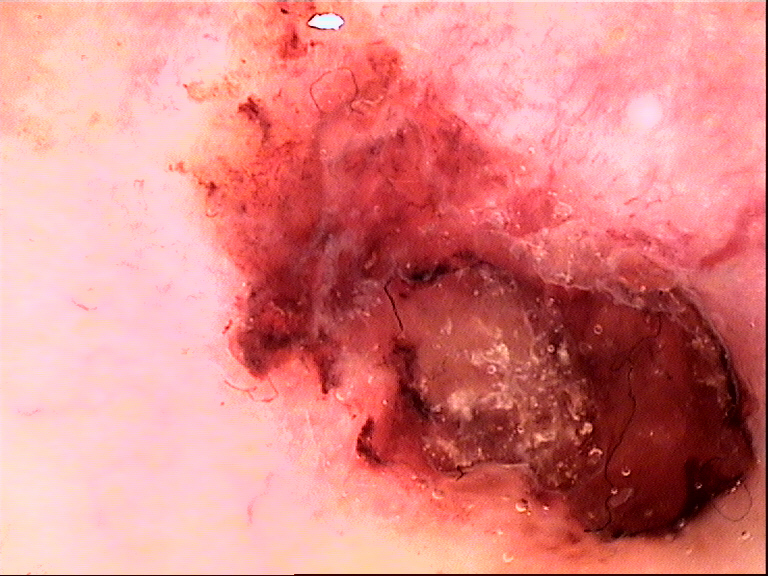<dermoscopy>
  <image>dermatoscopy</image>
  <lesion_type>
    <main_class>keratinocytic</main_class>
  </lesion_type>
  <diagnosis>
    <name>squamous cell carcinoma</name>
    <code>scc</code>
    <malignancy>malignant</malignancy>
    <super_class>non-melanocytic</super_class>
    <confirmation>histopathology</confirmation>
  </diagnosis>
</dermoscopy>